The photo was captured at an angle. The affected area is the arm:
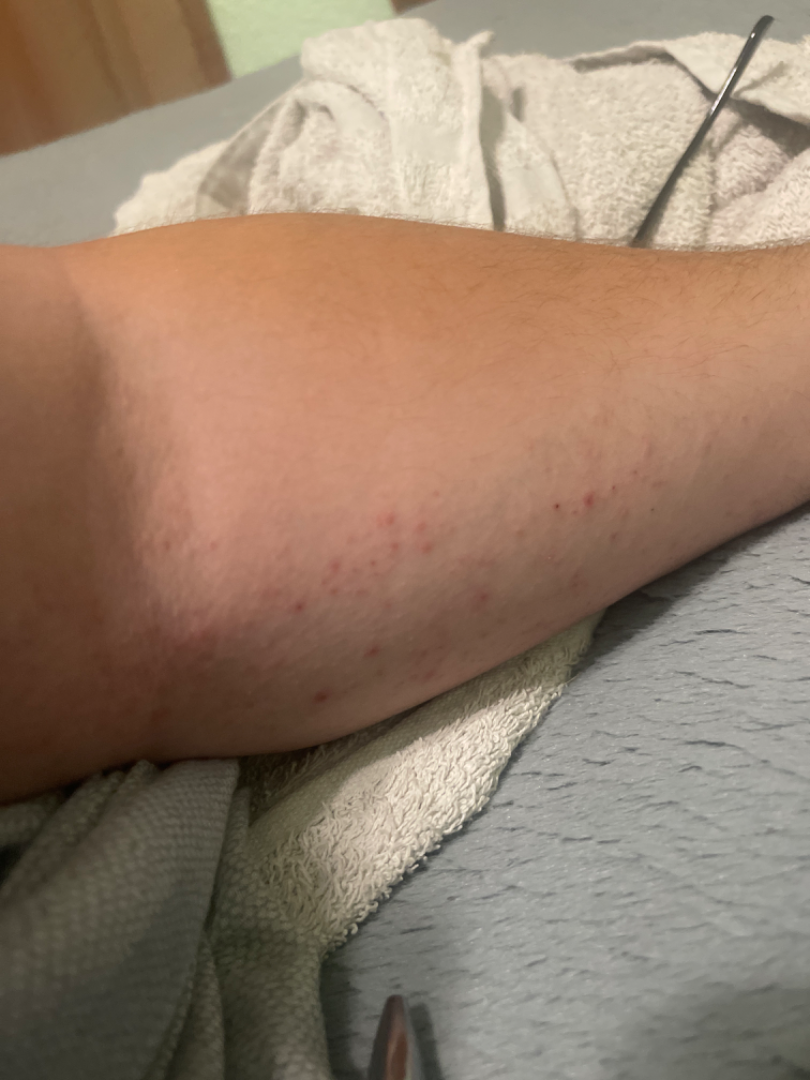No associated systemic symptoms reported.
Self-categorized by the patient as a rash.
The lesion is associated with itching.
On teledermatology review: in keeping with Eczema.